The subject is a female roughly 50 years of age. A dermoscopic view of a skin lesion — 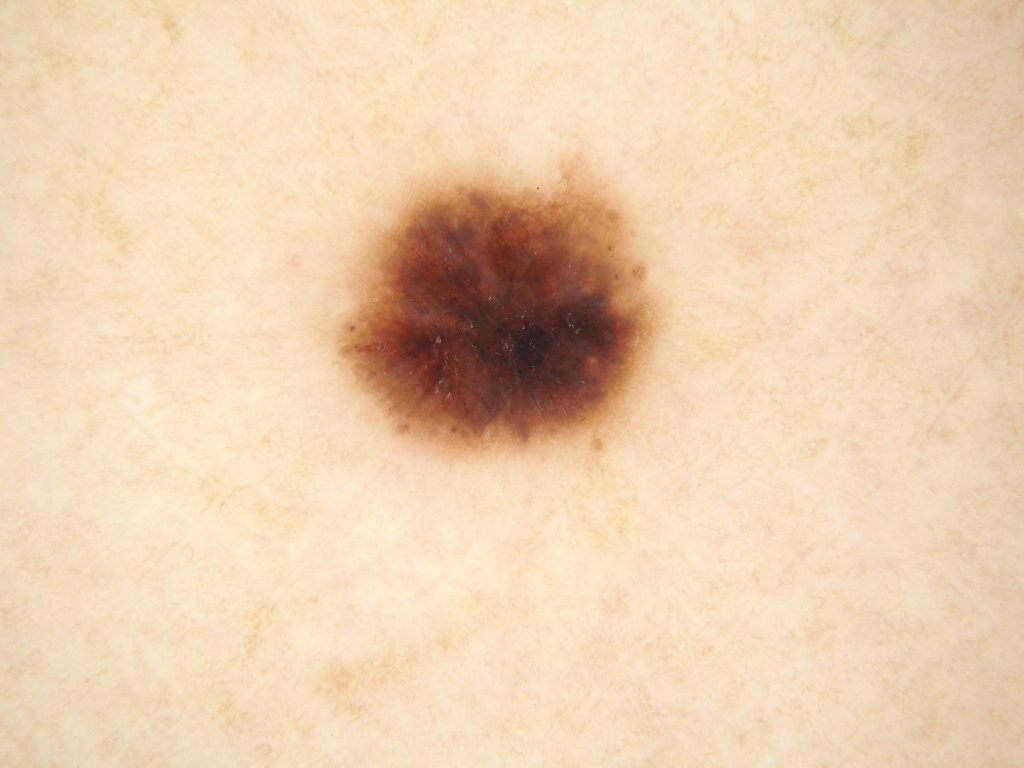Case summary: Dermoscopic review identifies globules and pigment network; no negative network, streaks, or milia-like cysts. With coordinates (x1, y1, x2, y2), the lesion occupies the region [333, 165, 662, 456]. Impression: The clinical diagnosis was a melanocytic nevus, a benign skin lesion.